This is a close-up image:
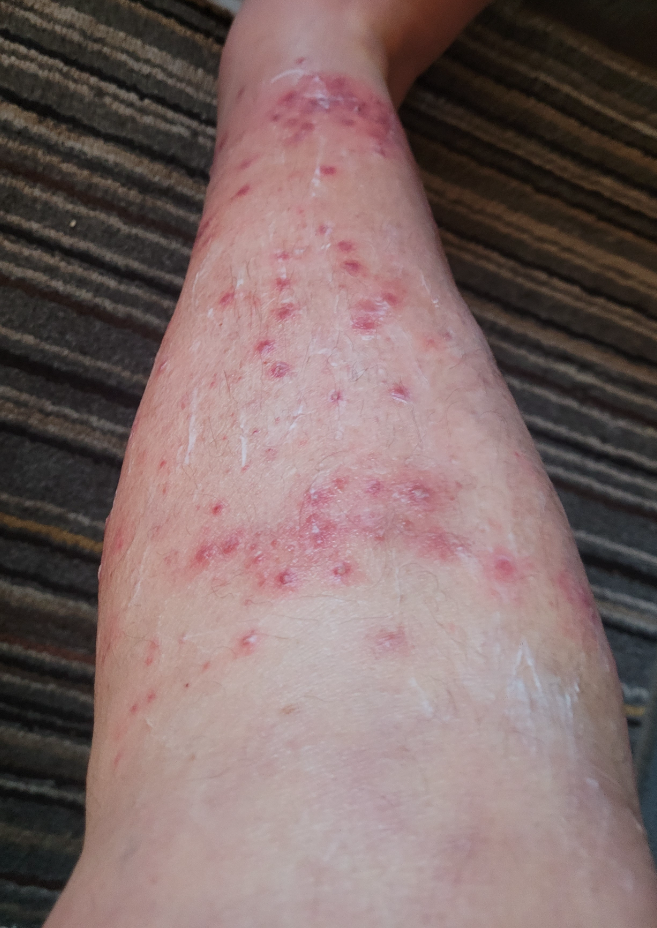Assessment:
Reviewed remotely by one dermatologist: most consistent with Insect Bite.